A dermatoscopic image of a skin lesion.
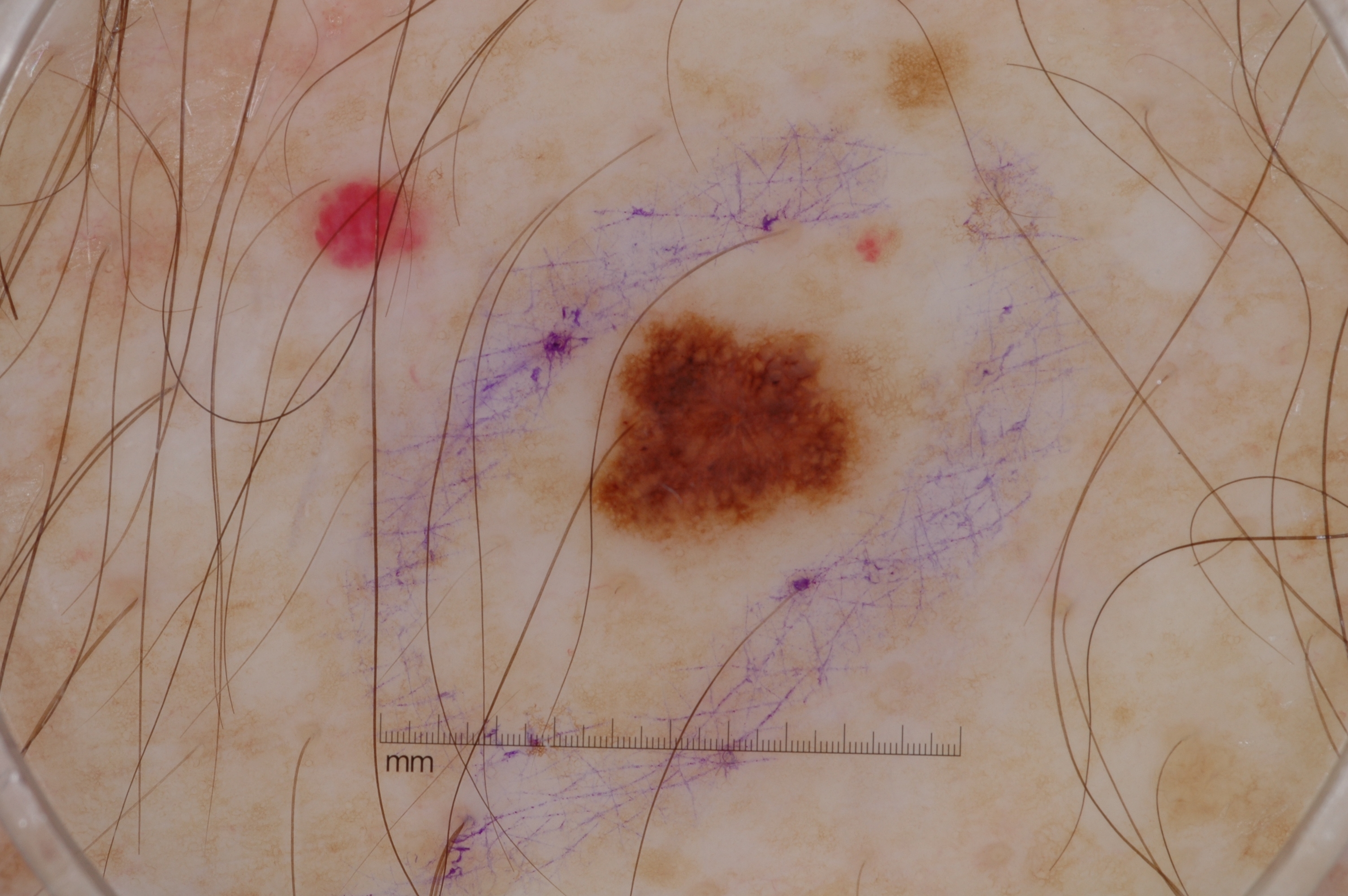location: [590,315,885,546]
impression: a melanoma, a malignancy